The patient considered this a rash · texture is reported as fluid-filled and flat · located on the front of the torso · this image was taken at an angle · present for less than one week · symptoms reported: itching and burning.
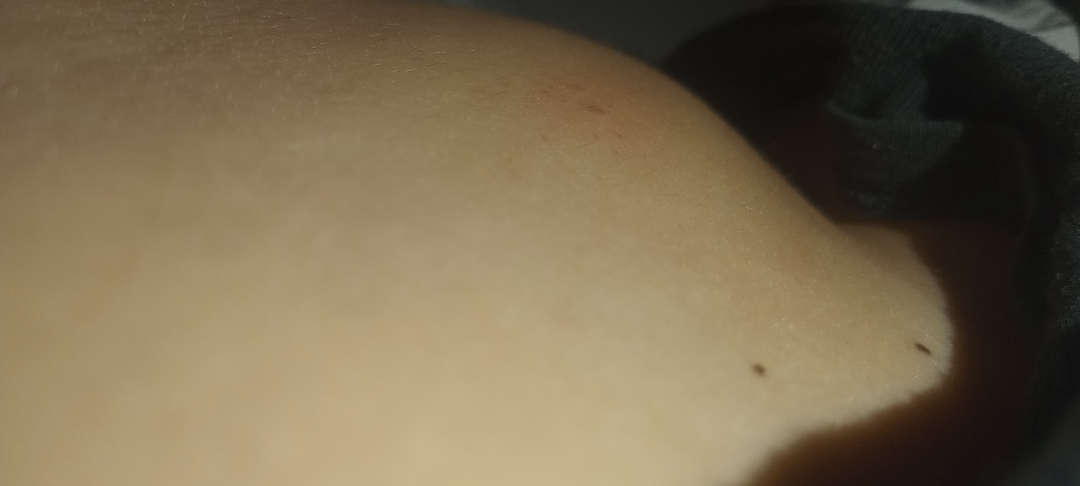assessment: could not be assessed